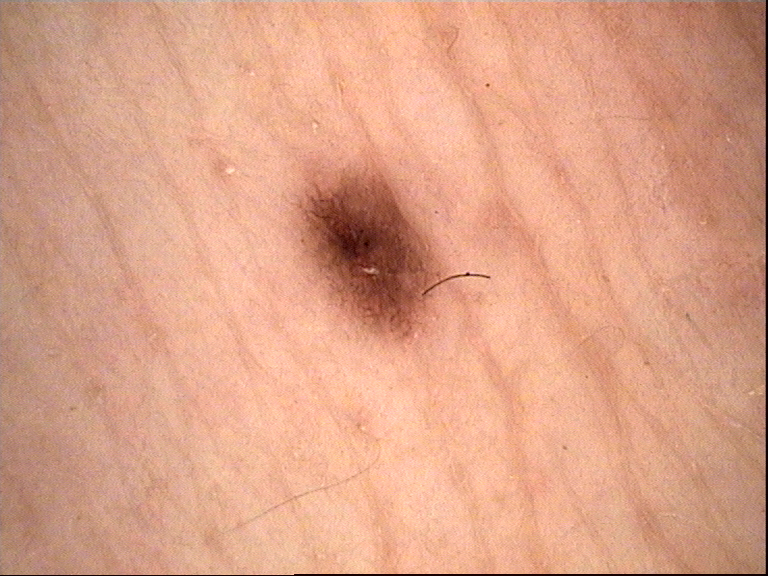{
  "image": "dermatoscopy",
  "diagnosis": {
    "name": "acral dysplastic junctional nevus",
    "code": "ajd",
    "malignancy": "benign",
    "super_class": "melanocytic",
    "confirmation": "expert consensus"
  }
}